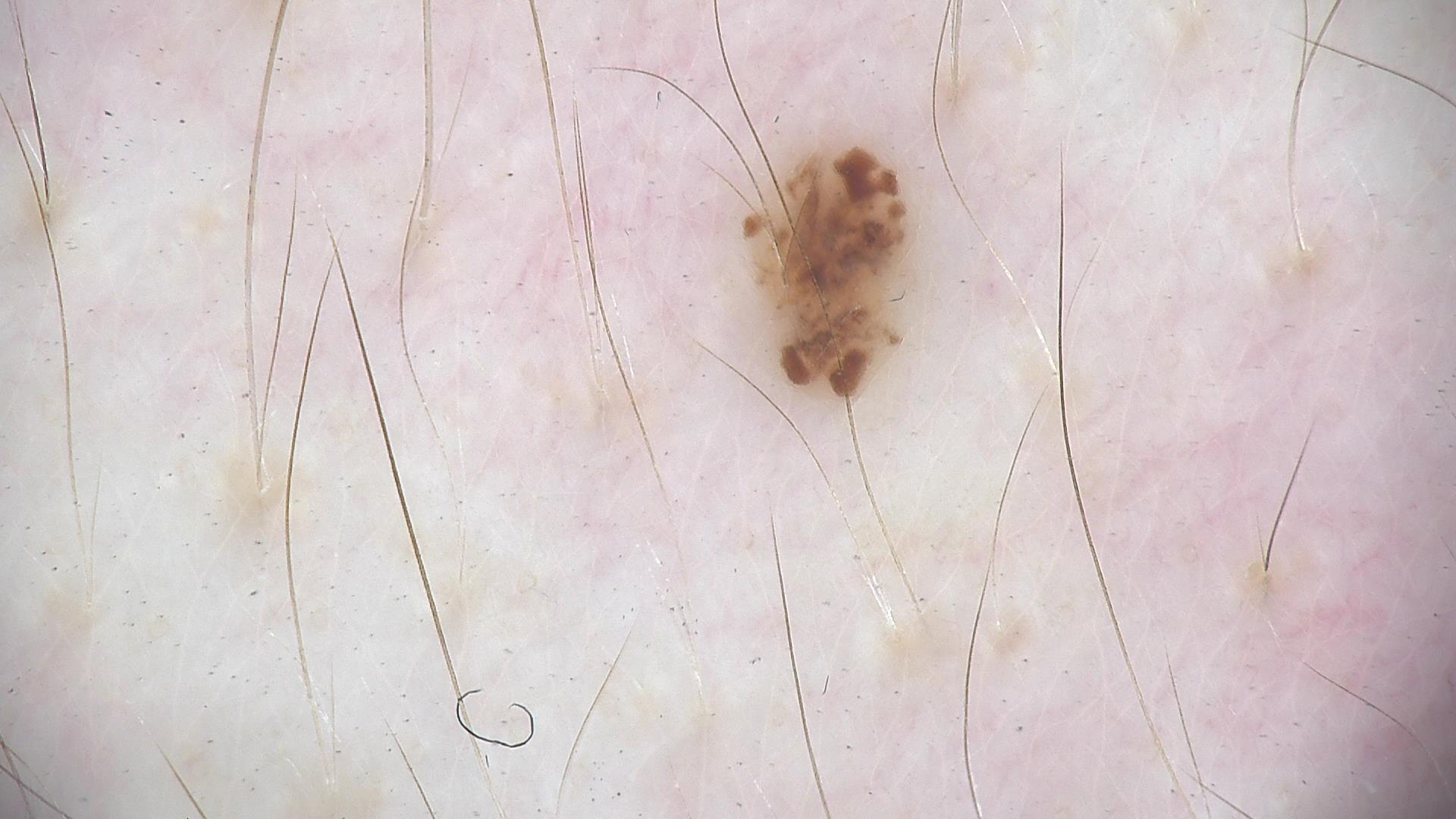Classified as a benign lesion — a dysplastic junctional nevus.